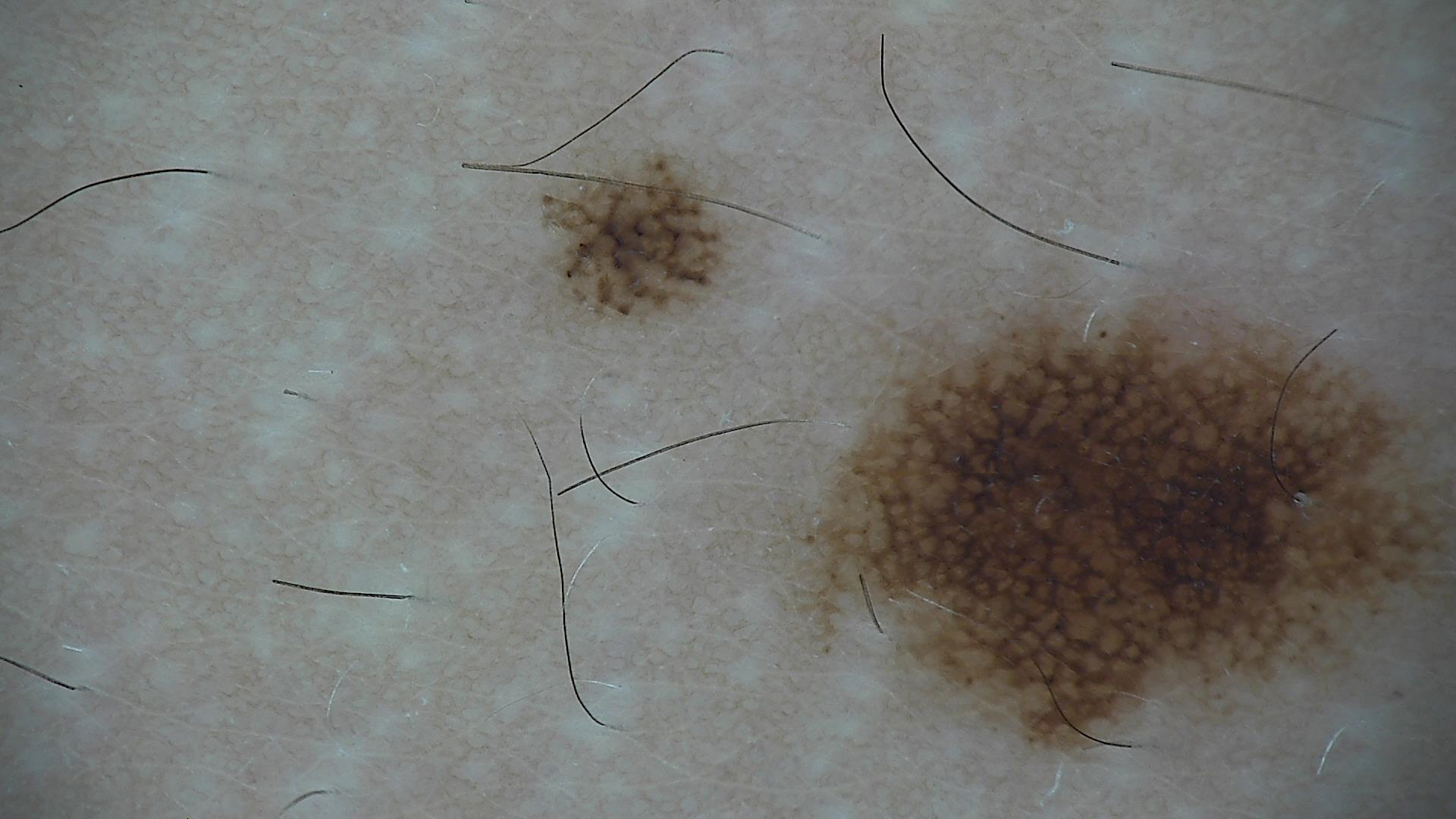image type = dermoscopy, assessment = dysplastic junctional nevus (expert consensus).